A male subject, aged 28 to 32; a dermoscopic view of a skin lesion.
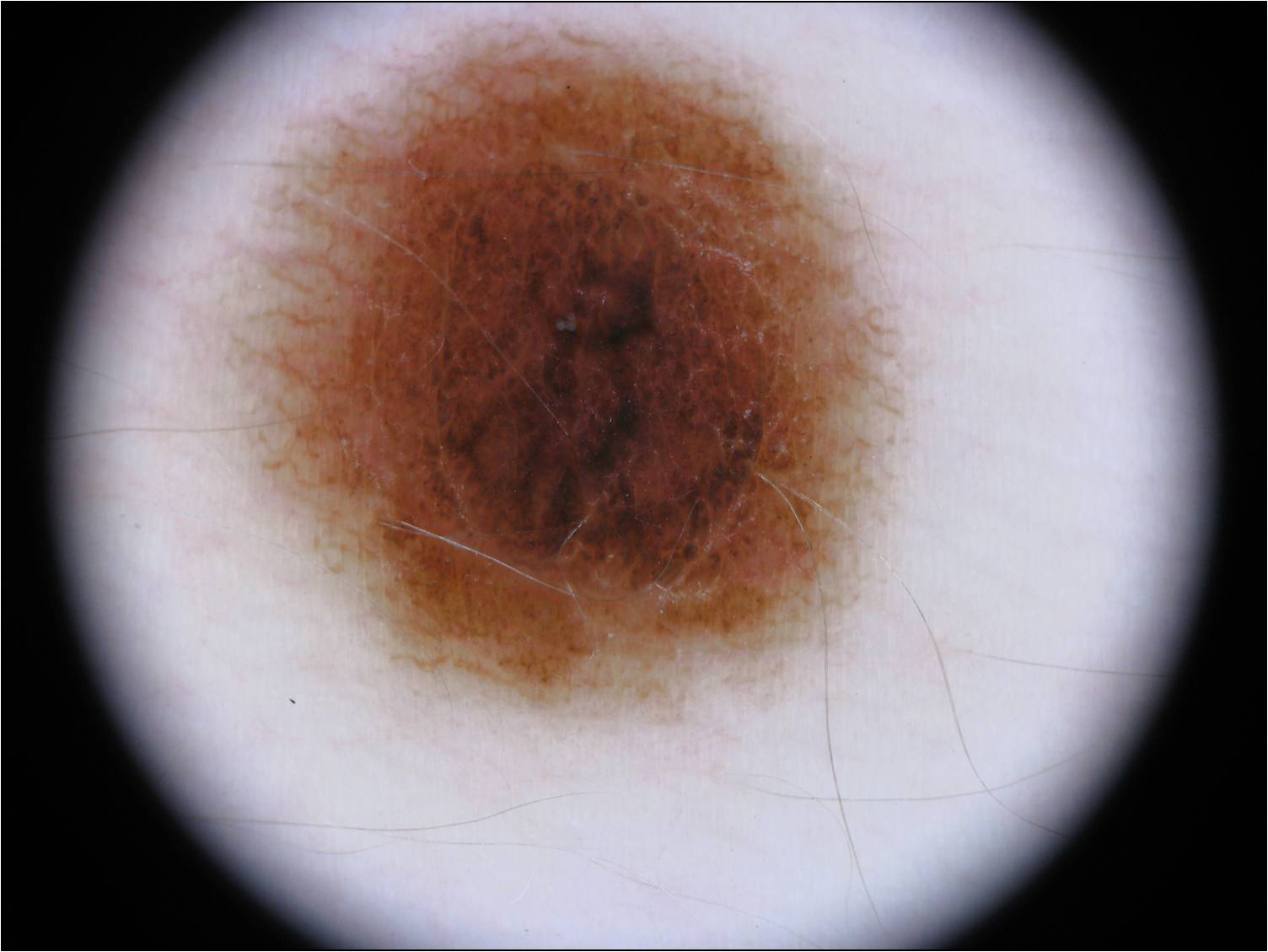Q: What is the lesion's bounding box?
A: 191/16/911/731
Q: What dermoscopic features are present?
A: globules, negative network, and streaks; absent: pigment network and milia-like cysts
Q: What did the assessment conclude?
A: a melanocytic nevus, a benign skin lesion